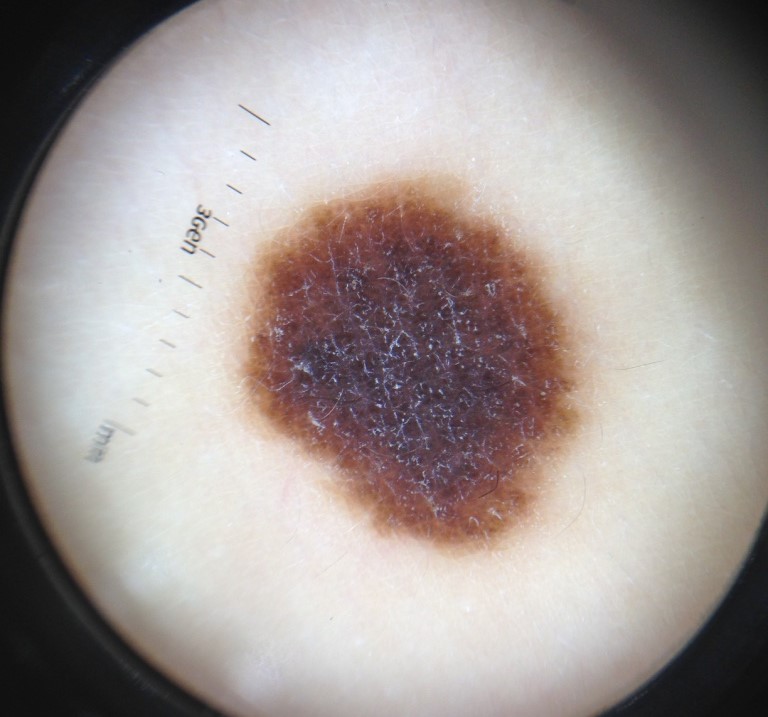Q: What is the diagnosis?
A: congenital compound nevus (expert consensus)